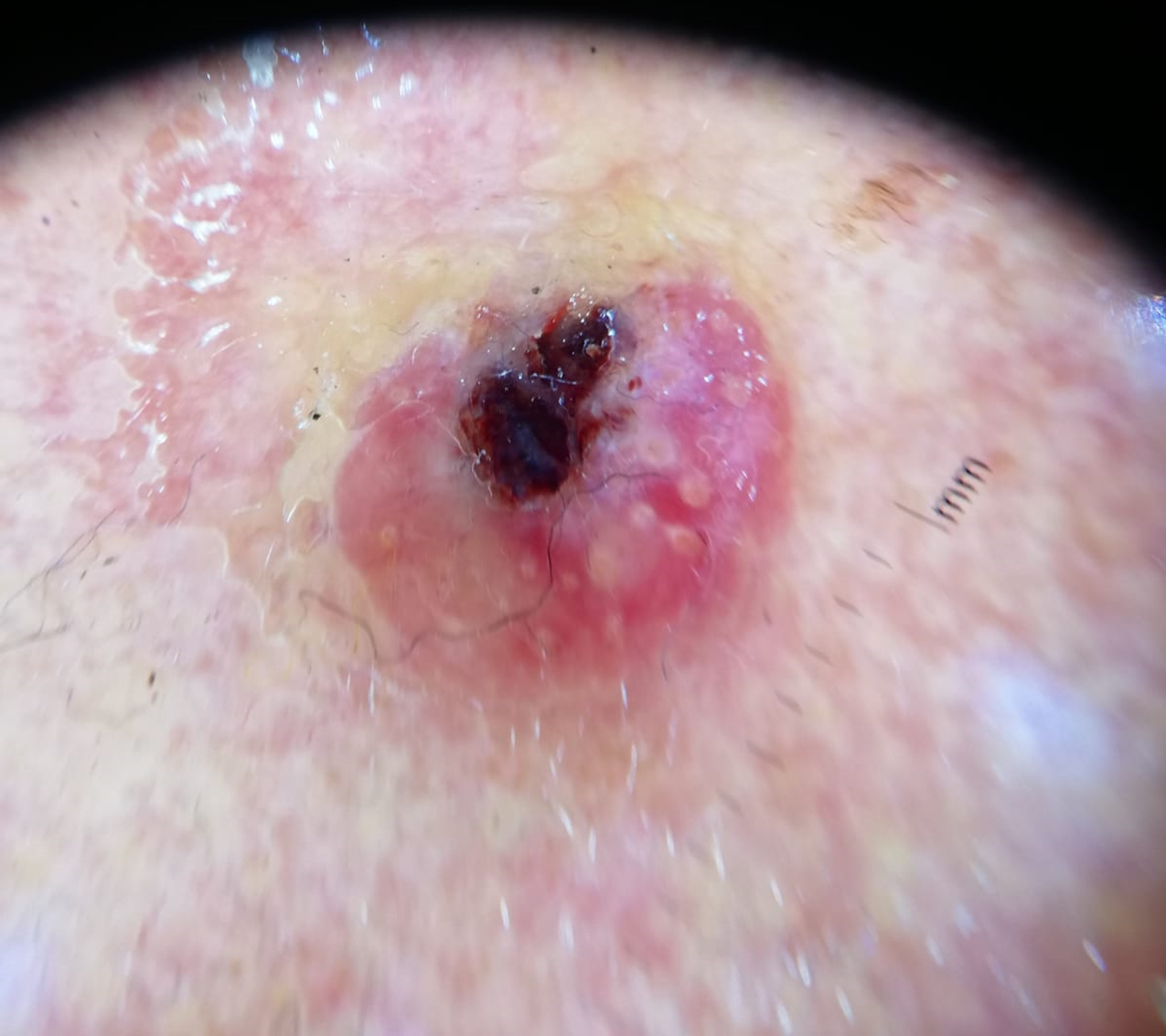Conclusion: Histopathologically confirmed as a squamous cell carcinoma.